A clinical photo of a skin lesion taken with a smartphone: 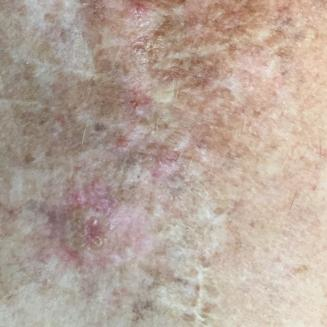Summary: The lesion is located on the chest. The patient reports that the lesion itches, has bled, and is elevated. Impression: Diagnosed by dermatologist consensus as a lesion with uncertain malignant potential — an actinic keratosis.